The contributor reports associated shortness of breath; the affected area is the top or side of the foot; the contributor is 30–39, female; the lesion is associated with itching, darkening and pain; the photo was captured at an angle.
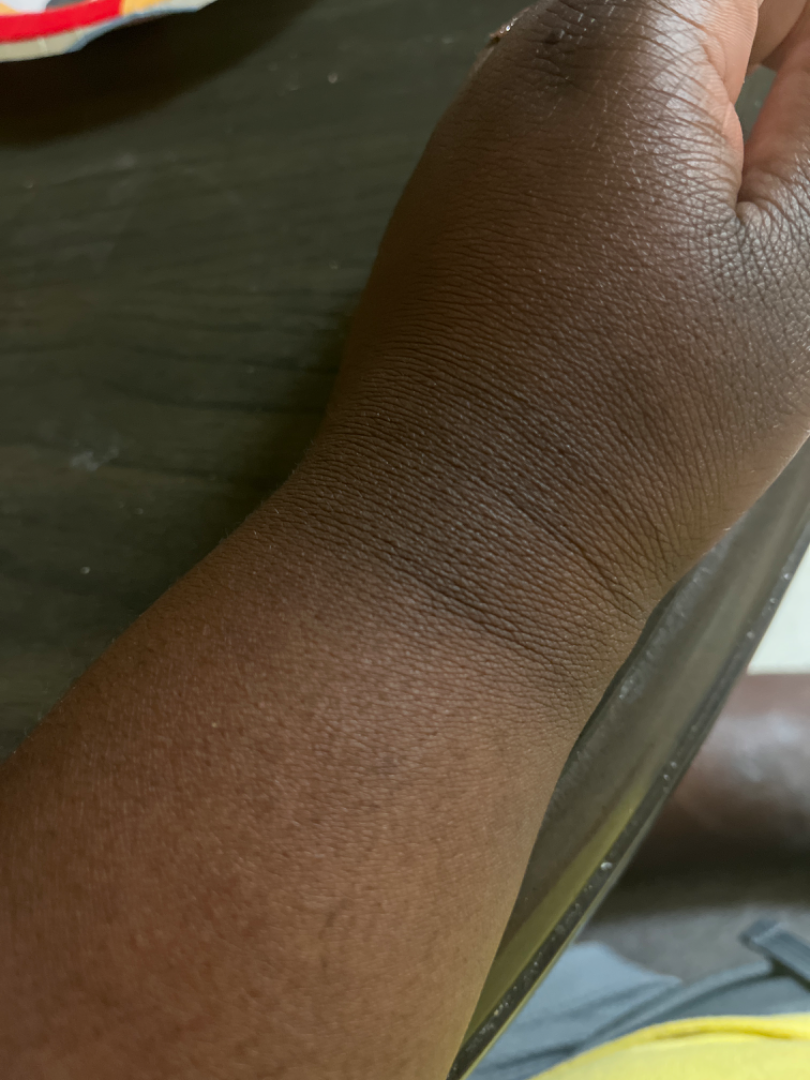<report>
<differential>
  <tied_lead>Tinea, Eczema</tied_lead>
  <unlikely>Psoriasis</unlikely>
</differential>
</report>